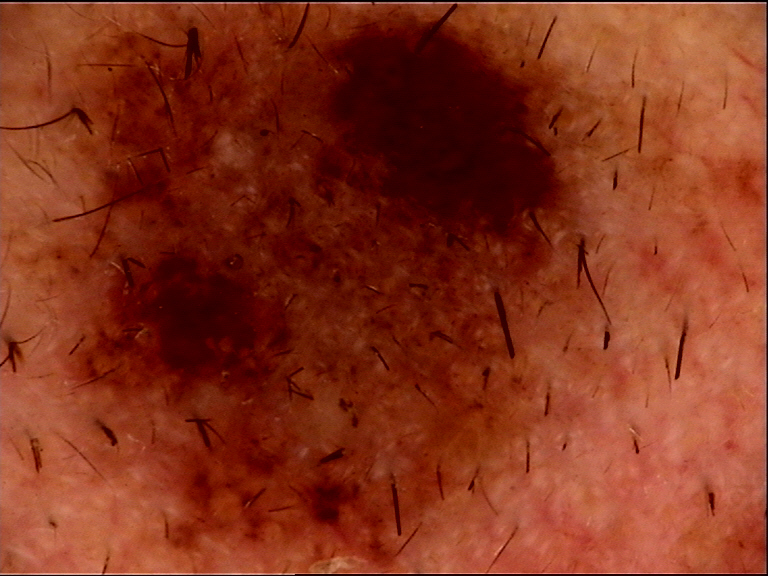Dermoscopy of a skin lesion. Labeled as a banal lesion — a congenital compound nevus.